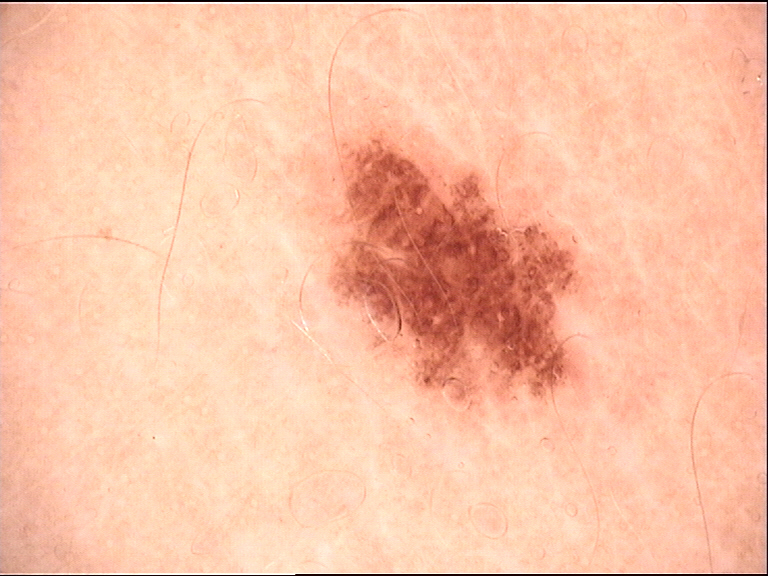A dermatoscopic image of a skin lesion. This is a banal lesion. Consistent with a junctional nevus.